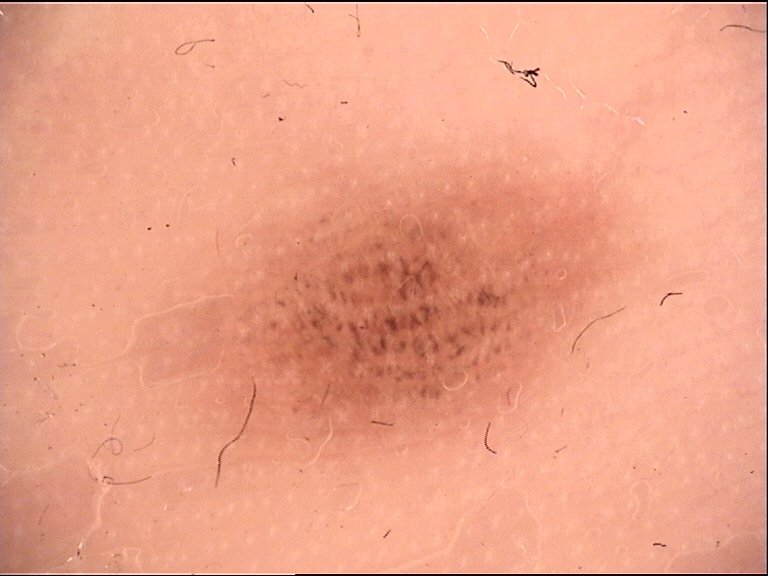Summary: A dermoscopic close-up of a skin lesion. Conclusion: Diagnosed as a banal lesion — an acral compound nevus.